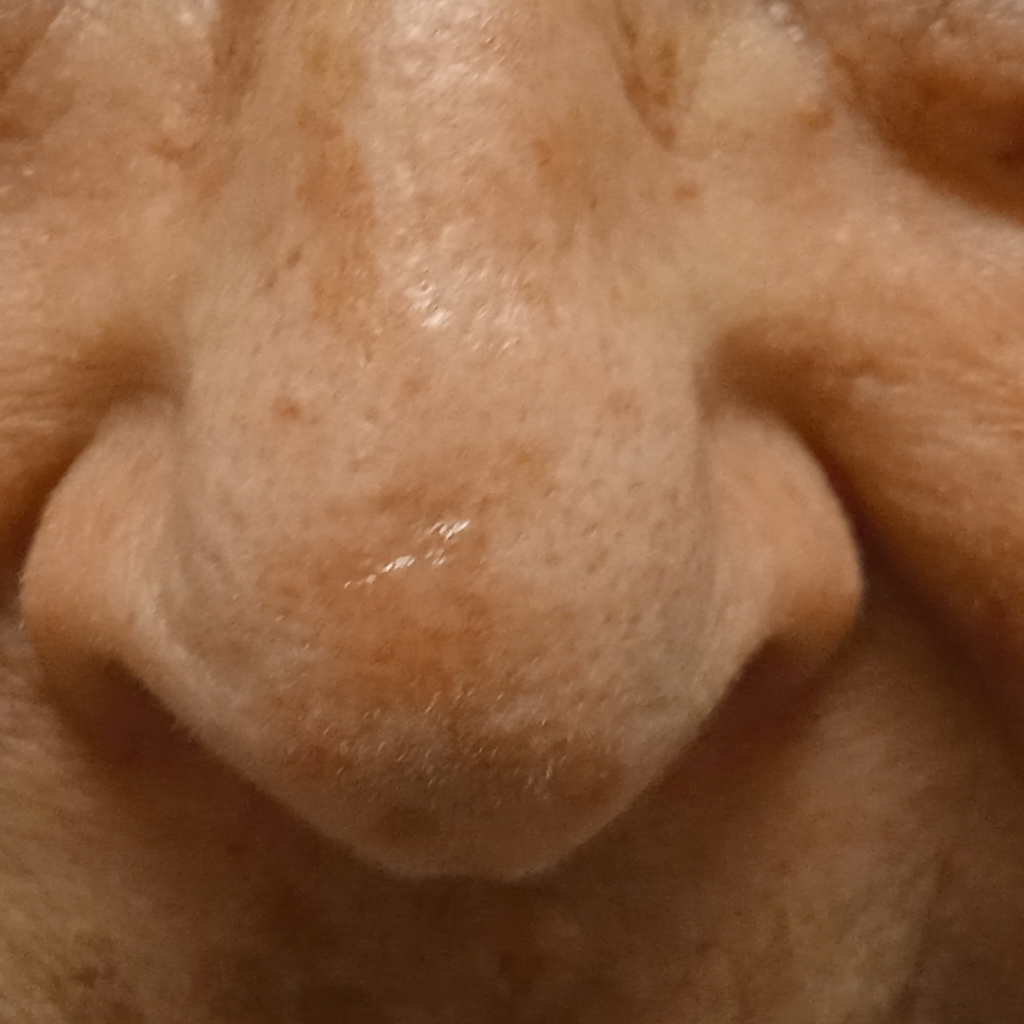{
  "patient": {
    "age": 84,
    "sex": "female"
  },
  "referral": "clinical suspicion of basal cell carcinoma",
  "sun_reaction": "skin tans without first burning",
  "mole_burden": "few melanocytic nevi overall",
  "image": "clinical photograph",
  "risk_factors": {
    "positive": [
      "a personal history of cancer"
    ]
  },
  "diagnosis": {
    "name": "basal cell carcinoma",
    "malignancy": "malignant",
    "procedure": "excision",
    "tumor_thickness_mm": 1.5
  }
}